Reported duration is one to four weeks · the patient is 18–29, female · located on the head or neck · the patient described the issue as a rash · the lesion is associated with enlargement, bothersome appearance and itching · an image taken at an angle · Fitzpatrick II — 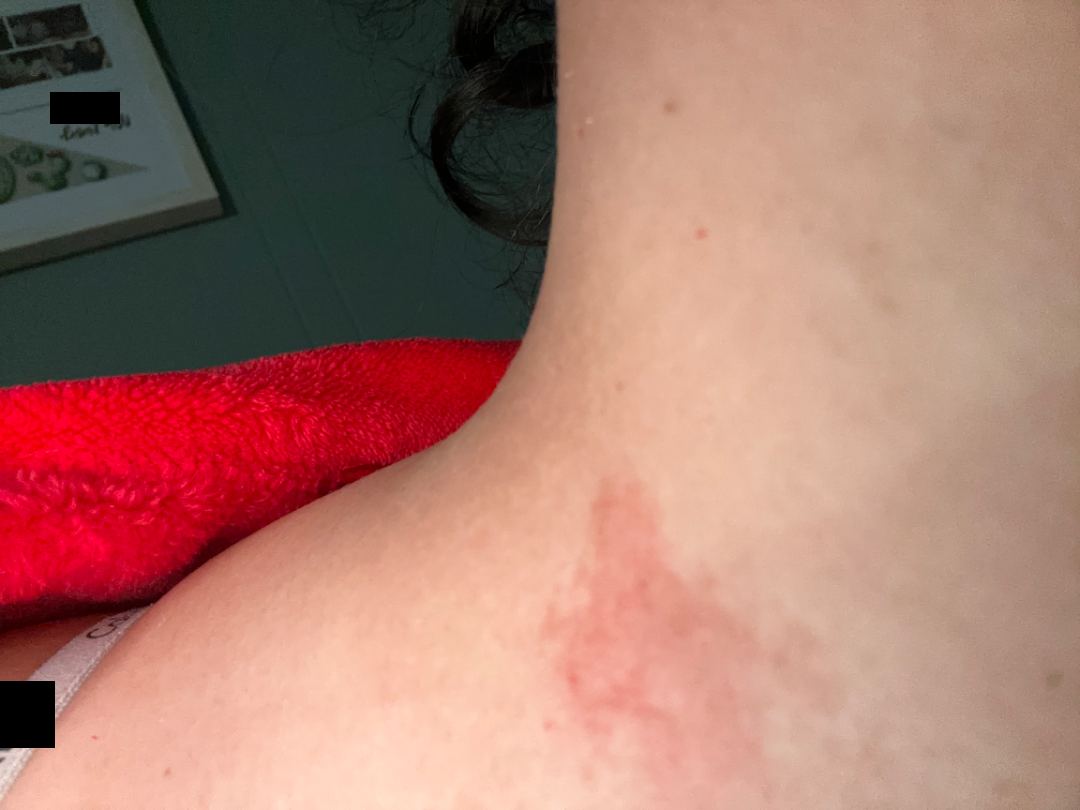On teledermatology review, Eczema (leading); Tinea (possible); Allergic Contact Dermatitis (possible).